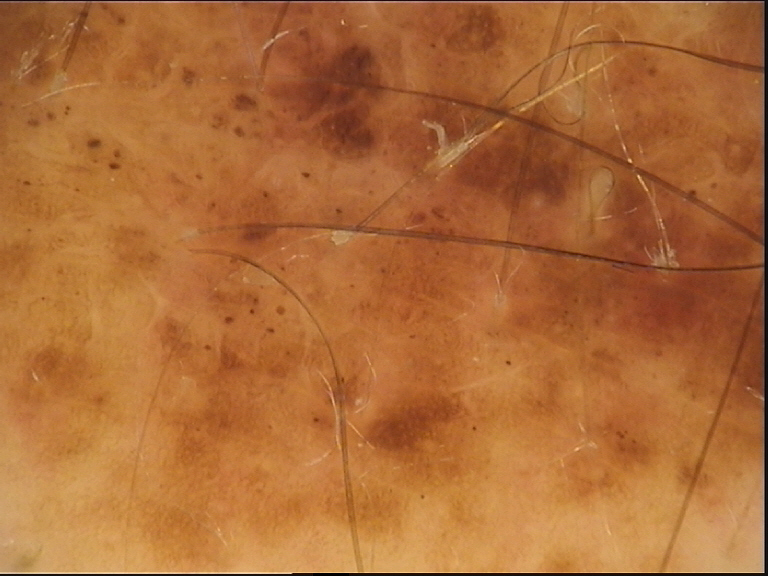modality: dermoscopy, lesion type: banal, diagnostic label: congenital compound nevus (expert consensus).